Symptoms reported: bothersome appearance and itching · female subject, age 18–29 · no constitutional symptoms were reported · the patient considered this a nail problem · the contributor reports the condition has been present for three to twelve months · the photo was captured at an angle · the lesion is described as rough or flaky:
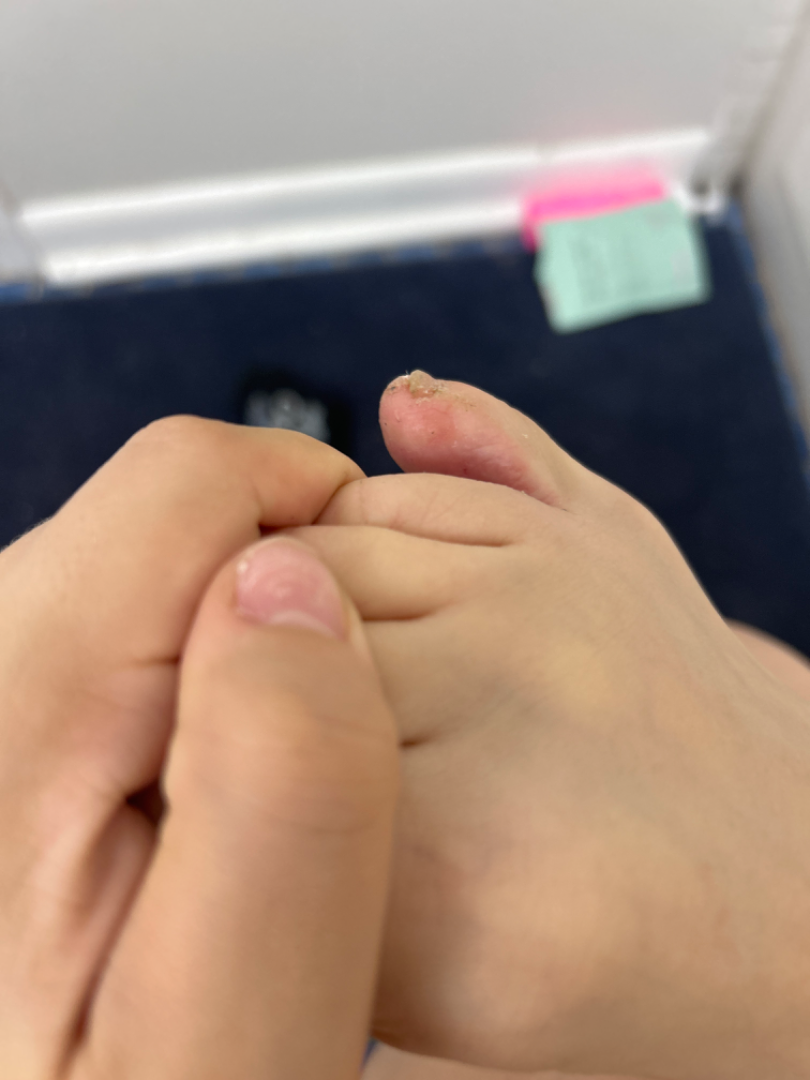| field | value |
|---|---|
| assessment | not assessable |